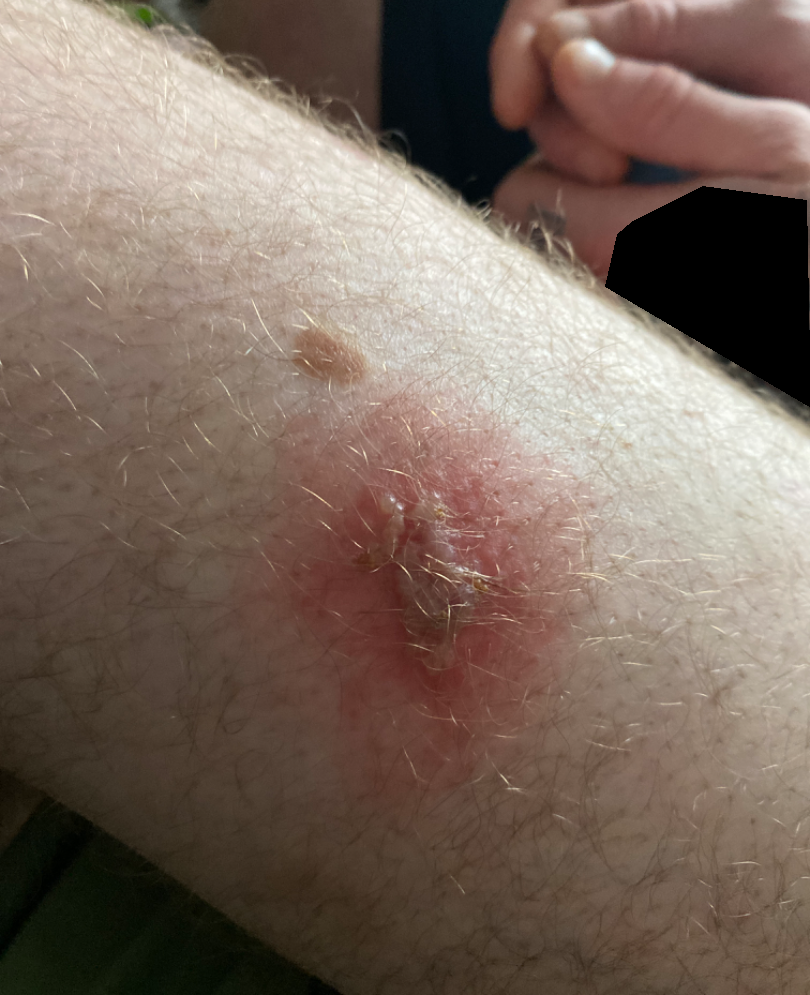This image was taken at an angle.
The patient also reports fever.
Located on the leg.
The condition has been present for less than one week.
The patient described the issue as a rash.
Reviewed remotely by one dermatologist: favoring Impetigo; possibly Secondary impetiginization.